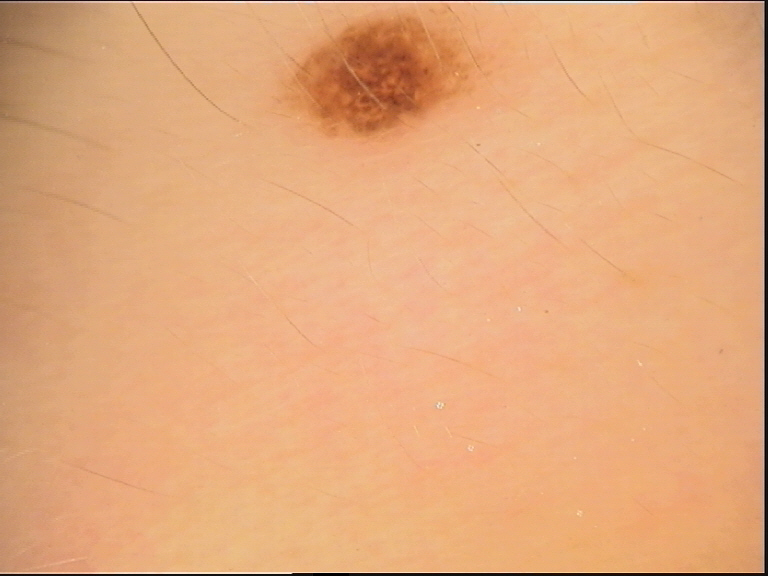A dermoscopic image of a skin lesion. Consistent with a dysplastic compound nevus.